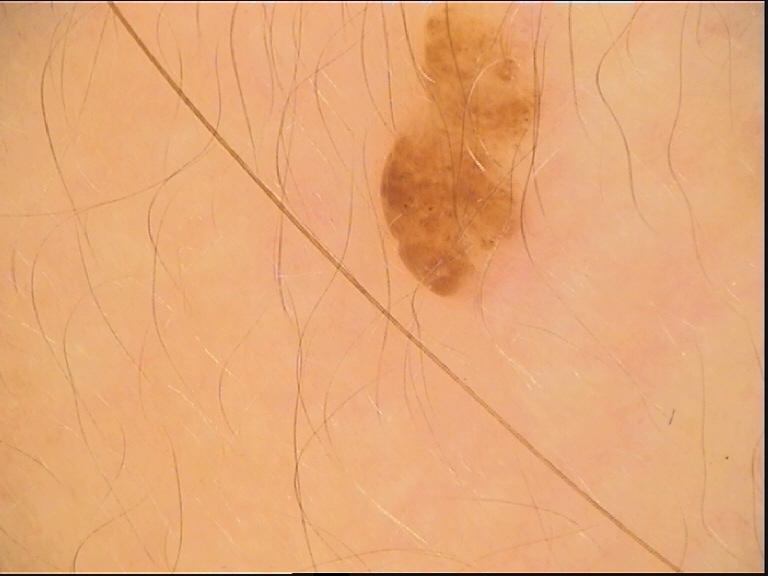The morphology is that of a keratinocytic lesion.
Diagnosed as a benign lesion — a seborrheic keratosis.